The photograph was taken at an angle; the affected area is the leg — 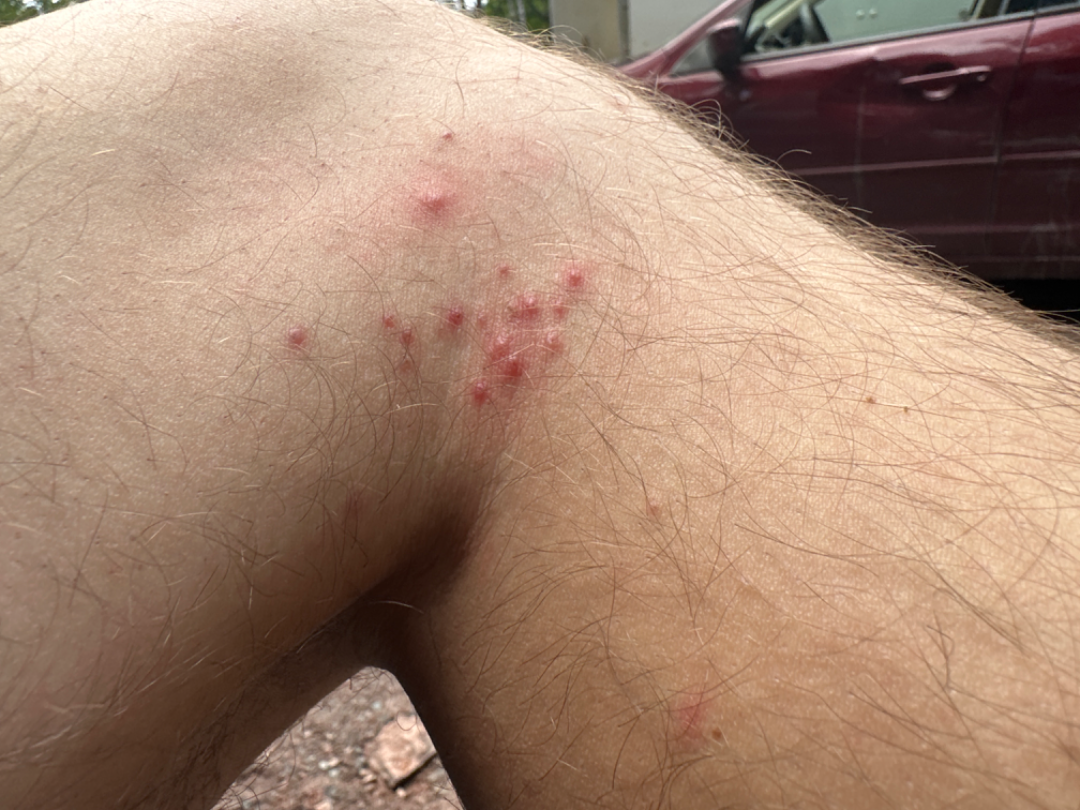Review: The case was indeterminate on photographic review.